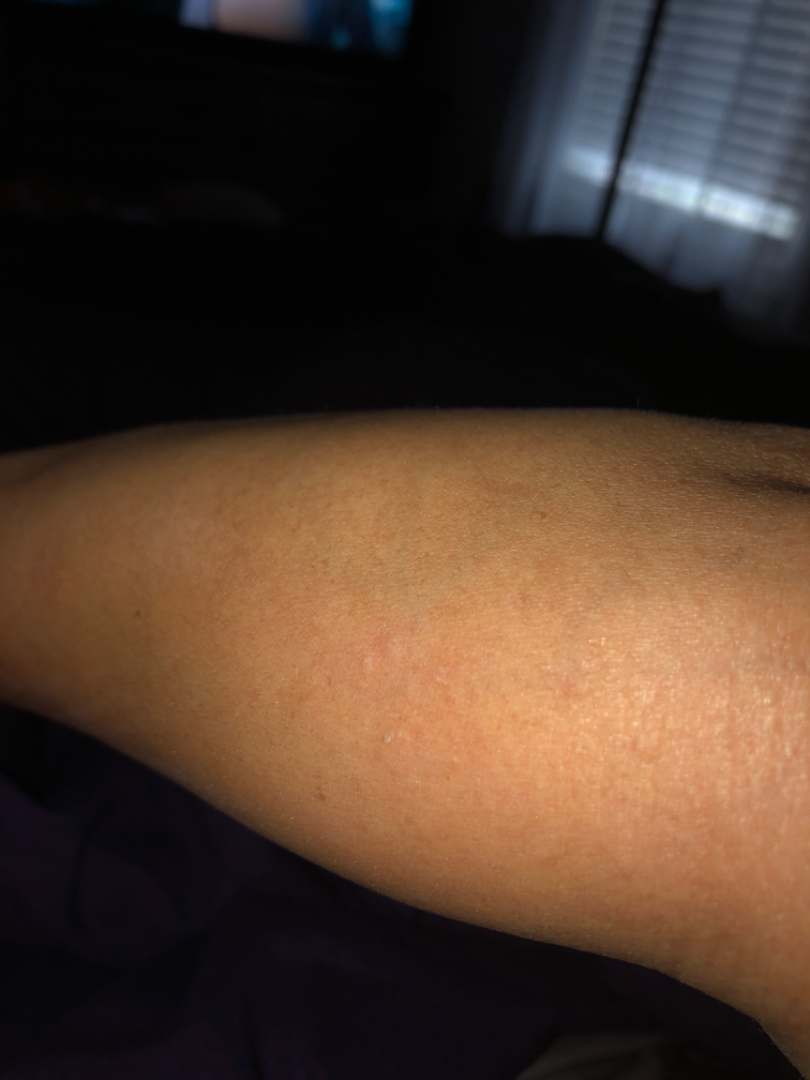<report>
  <assessment>unable to determine</assessment>
  <duration>one to four weeks</duration>
  <patient>female, age 40–49</patient>
  <shot_type>at a distance</shot_type>
  <body_site>arm</body_site>
</report>